This is a close-up image · male subject, age 18–29 · reported lesion symptoms include bothersome appearance and enlargement · the condition has been present for one to four weeks · the arm is involved · the patient indicates the lesion is raised or bumpy: 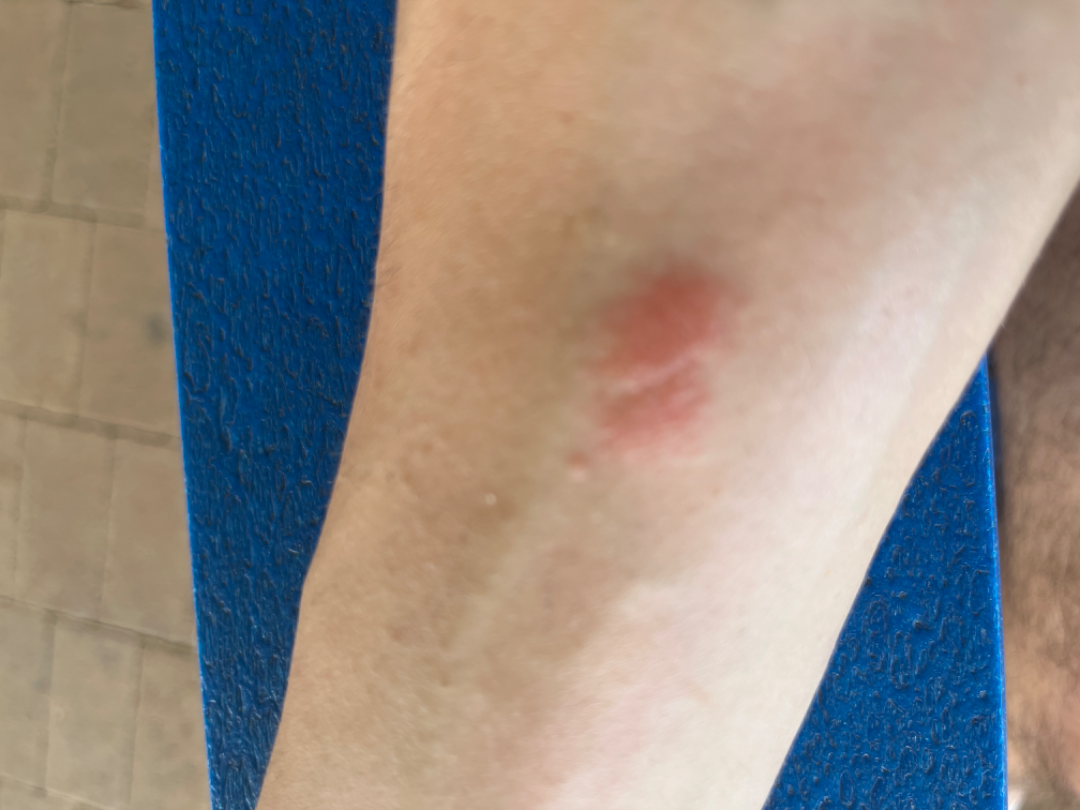Review: The skin findings could not be characterized from the image.